The lesion is described as rough or flaky · located on the arm and leg · the patient described the issue as a rash · the subject is 40–49, male · the photo was captured at an angle · symptoms reported: itching — 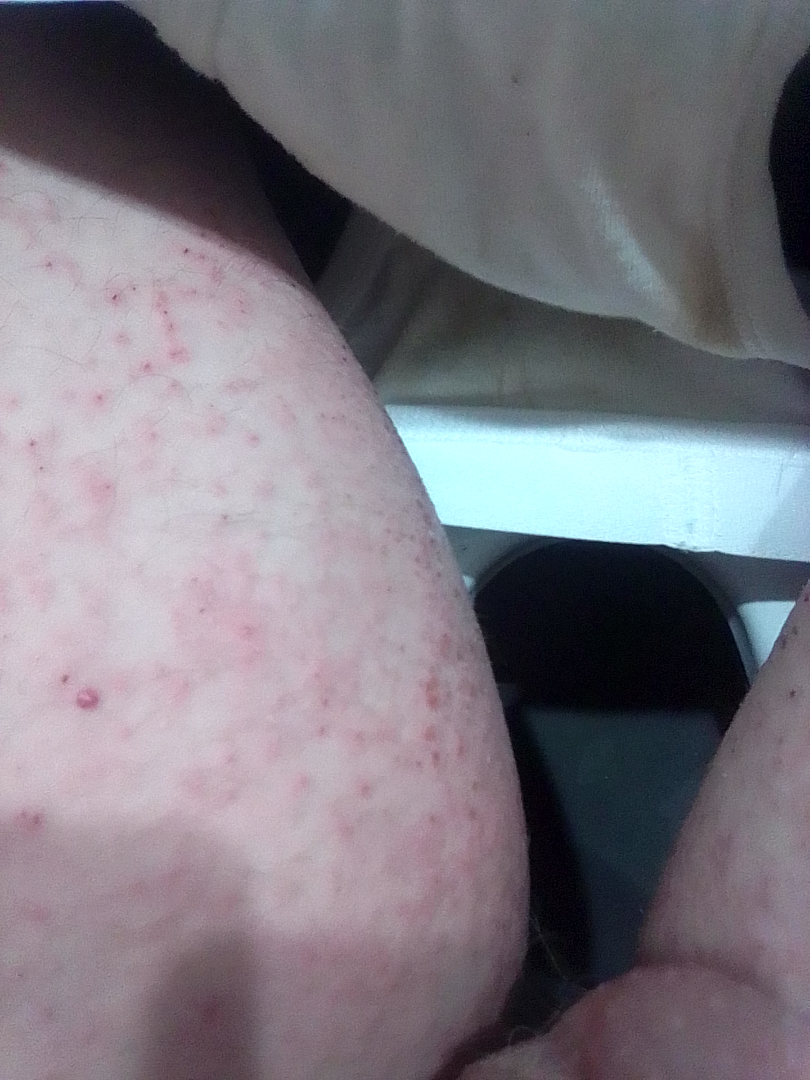dermatologist impression — consistent with Eczema.